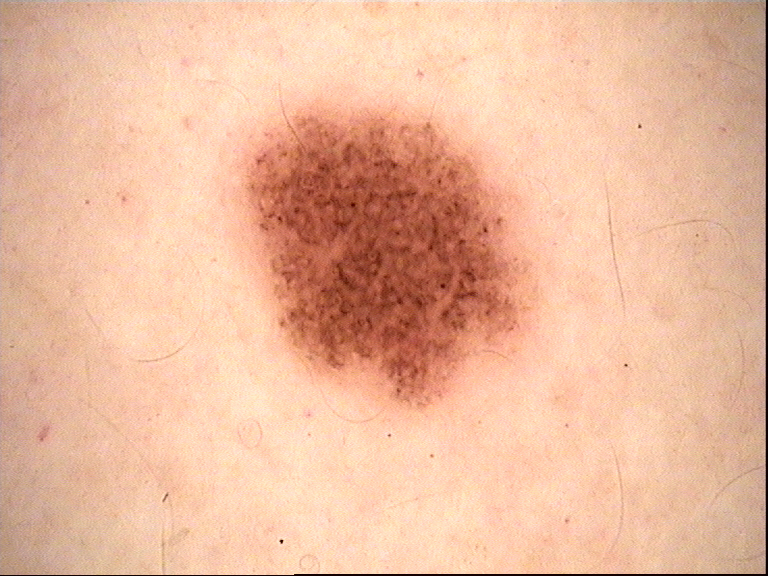class=dysplastic junctional nevus (expert consensus)